A female patient, aged around 45. A dermoscopic image of a skin lesion.
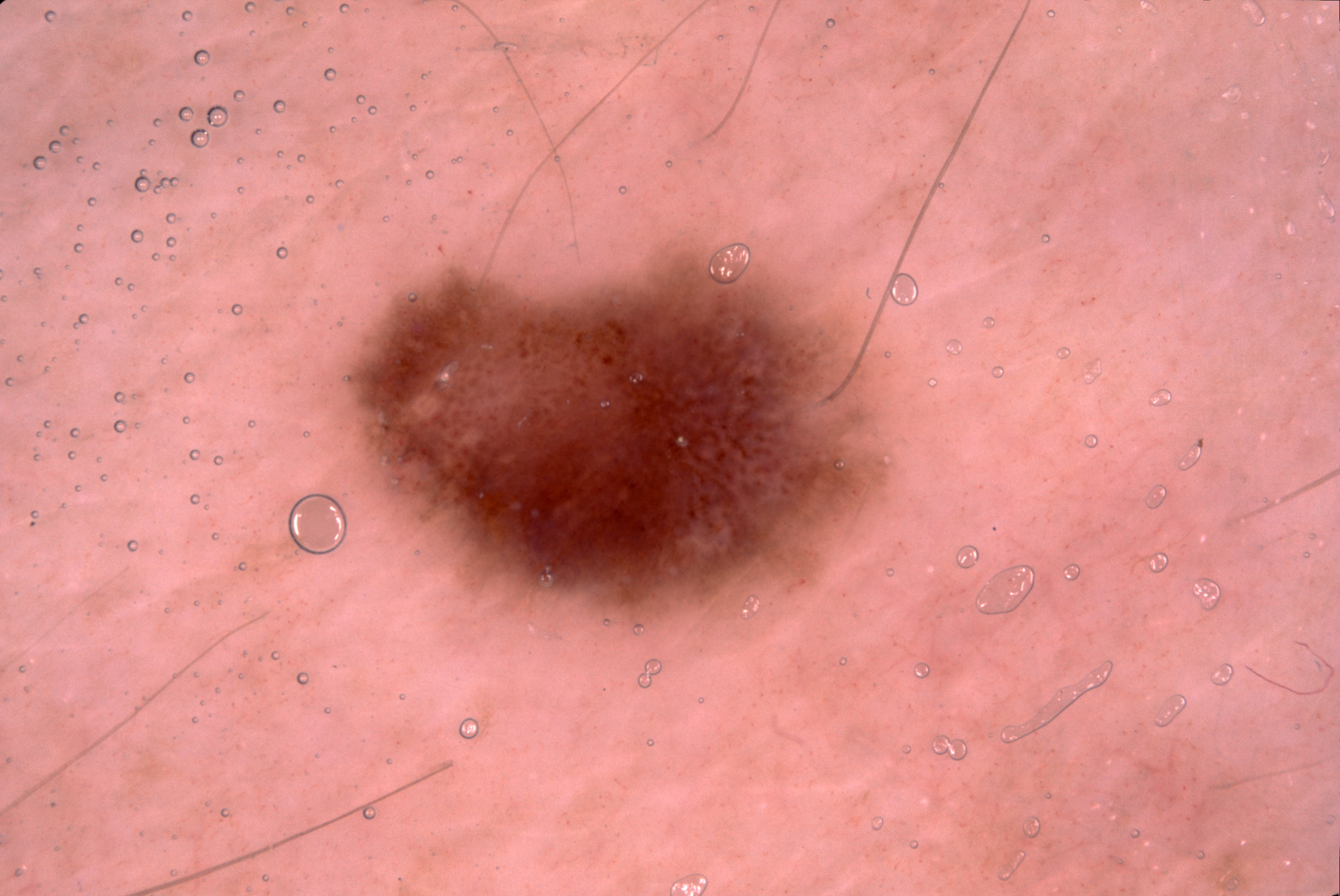A moderately sized lesion. Dermoscopically, the lesion shows negative network. As (left, top, right, bottom), the lesion's extent is bbox(318, 227, 896, 638). Consistent with a melanocytic nevus.